A skin lesion imaged with a dermatoscope: 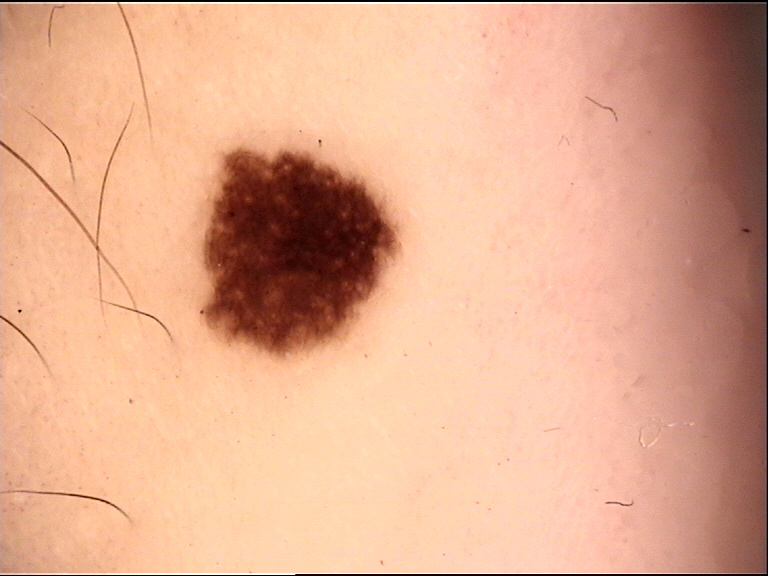Q: What is the diagnosis?
A: dysplastic junctional nevus (expert consensus)